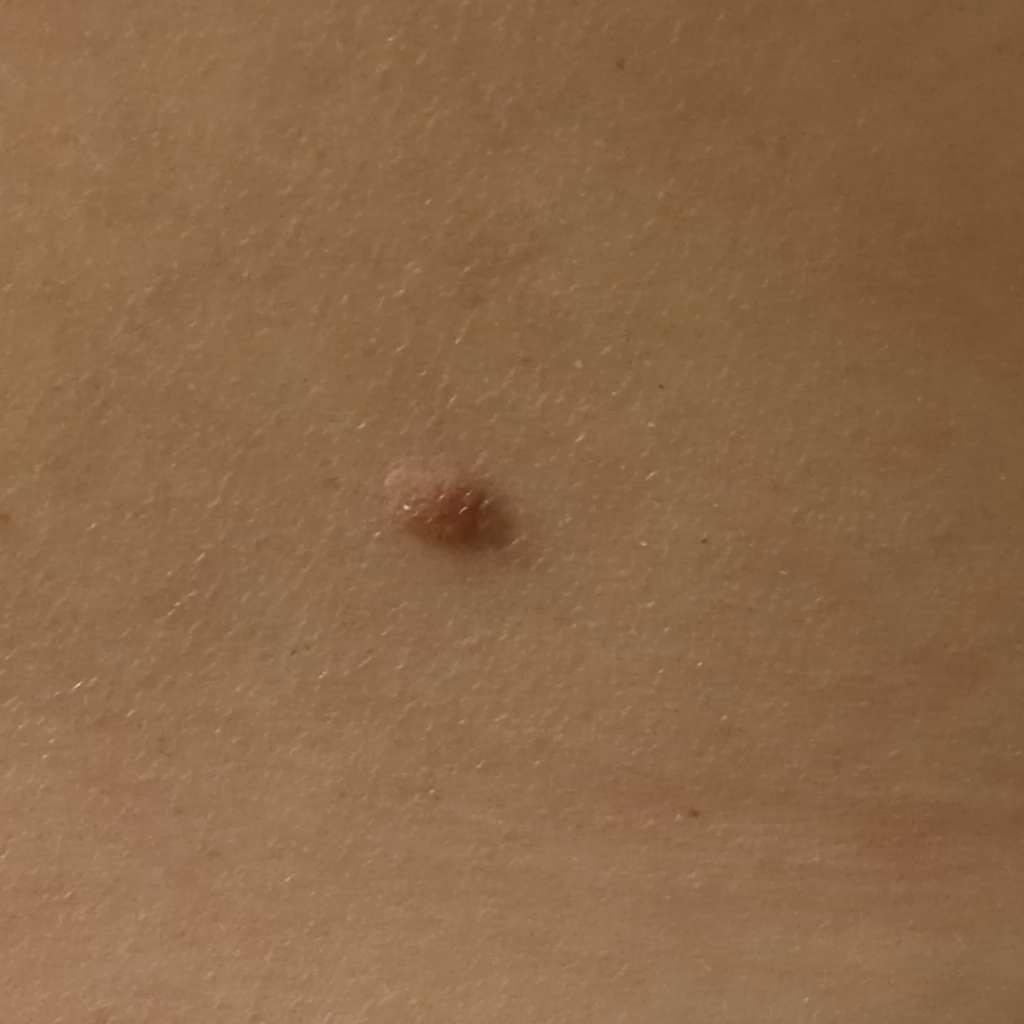Case summary: A macroscopic clinical photograph of a skin lesion. Referred with a clinical suspicion of basal cell carcinoma. A female patient 48 years old. Located on the back. Conclusion: Confirmed on histopathology as a basal cell carcinoma, following excision, with a measured tumor thickness of 1.1 mm.